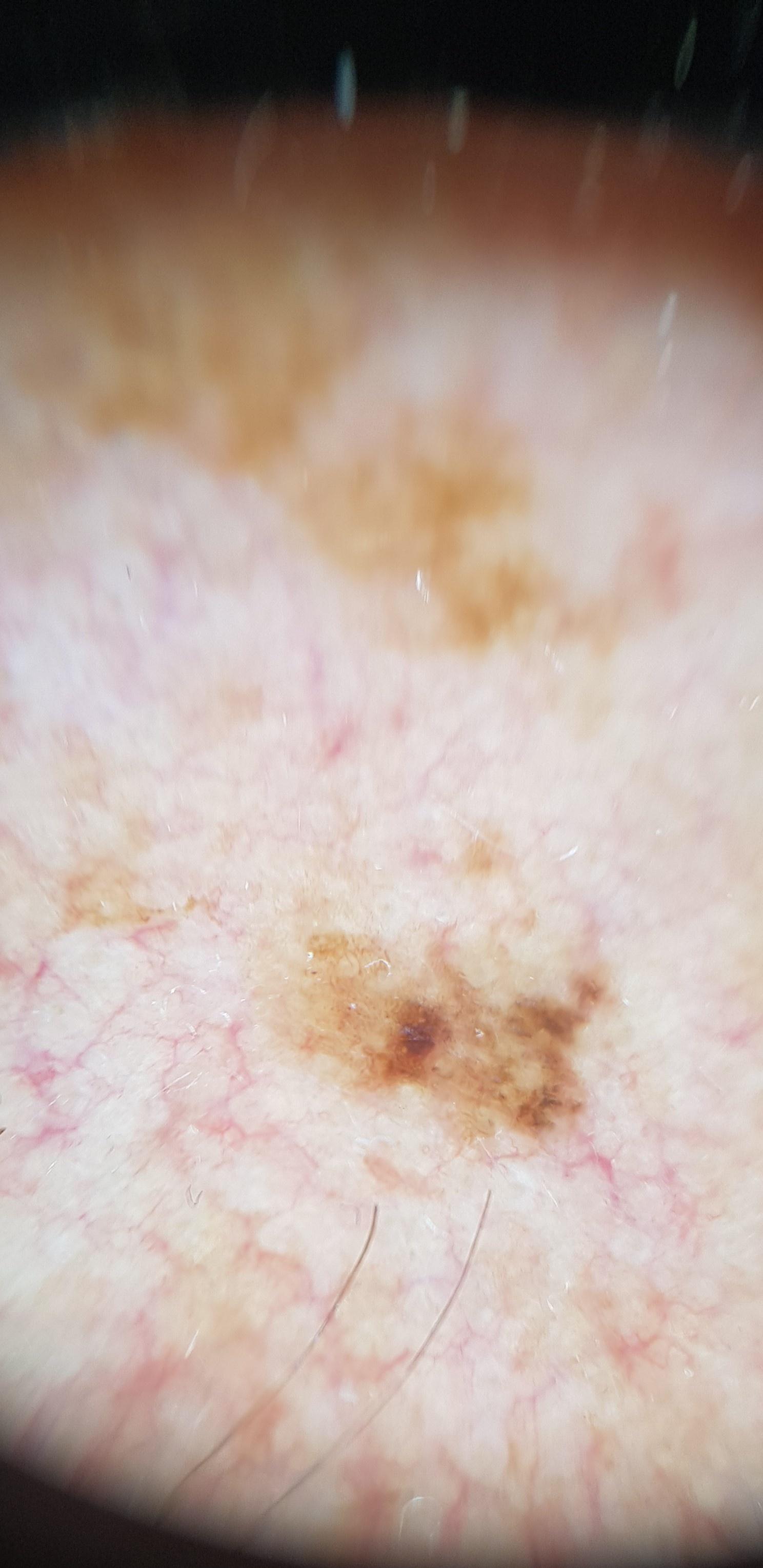Case:
* skin phototype · II
* melanoma history · a prior melanoma
* subject · male, about 65 years old
* location · the head or neck
* diagnosis · Melanoma (biopsy-proven)